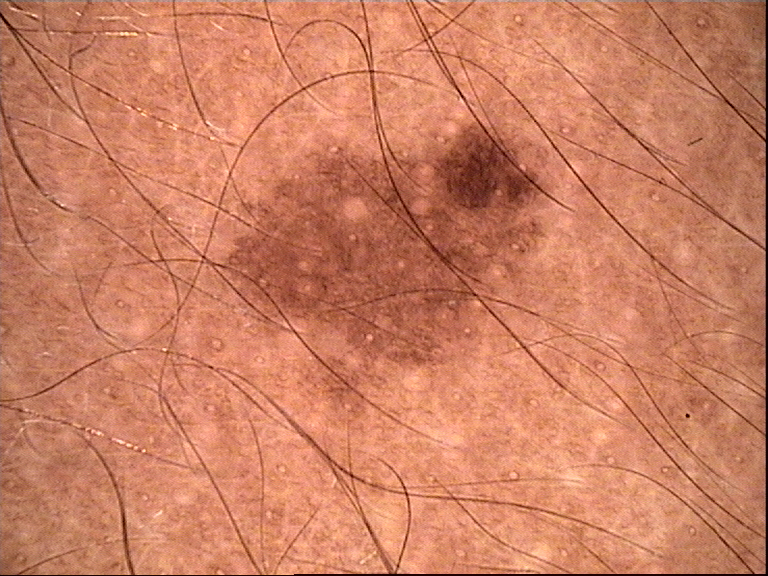A dermoscopic close-up of a skin lesion. Labeled as a benign lesion — a dysplastic junctional nevus.